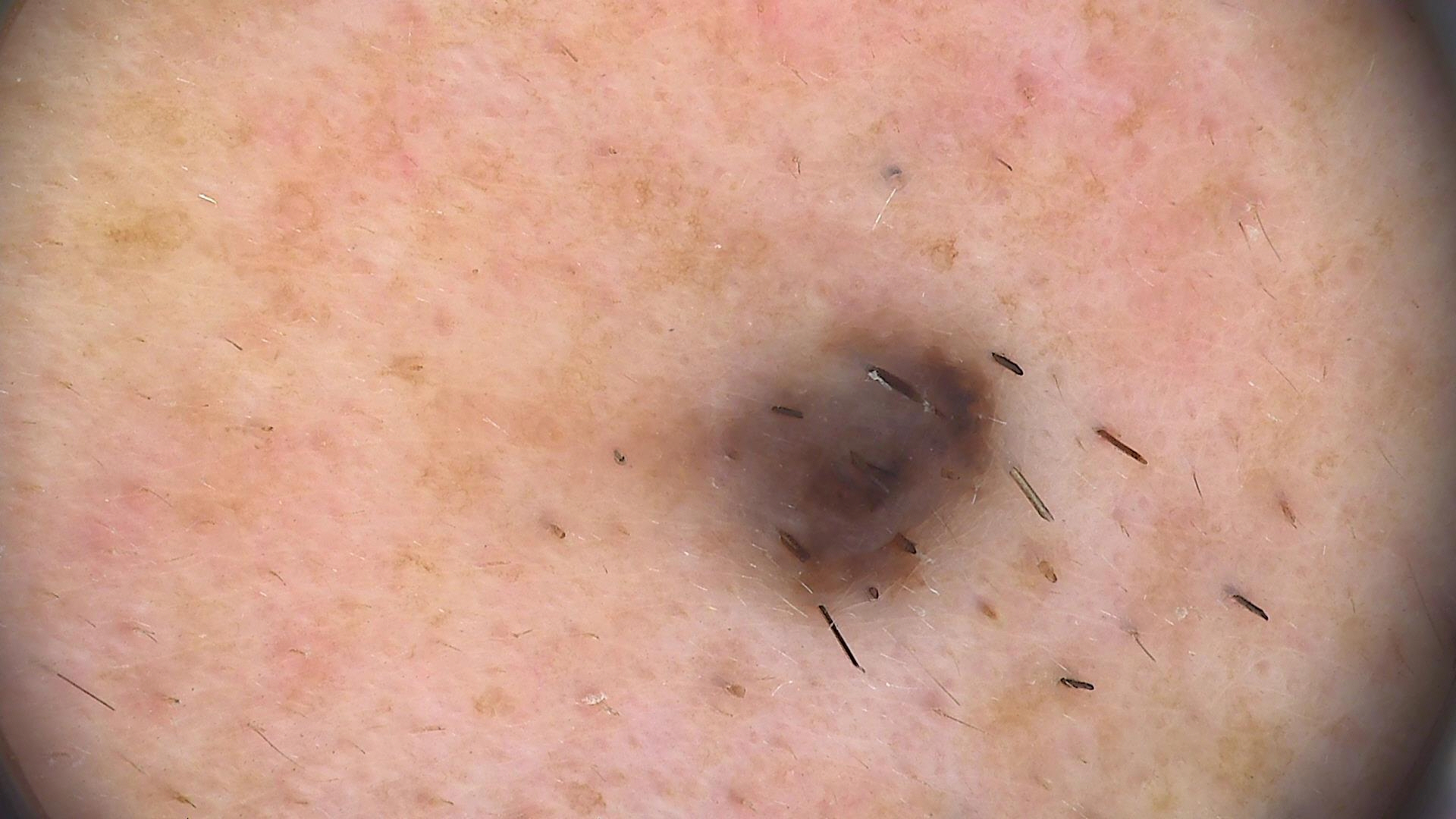A skin lesion imaged with a dermatoscope. The morphology is that of a banal lesion. Consistent with a compound nevus.